A dermoscopic image of a skin lesion.
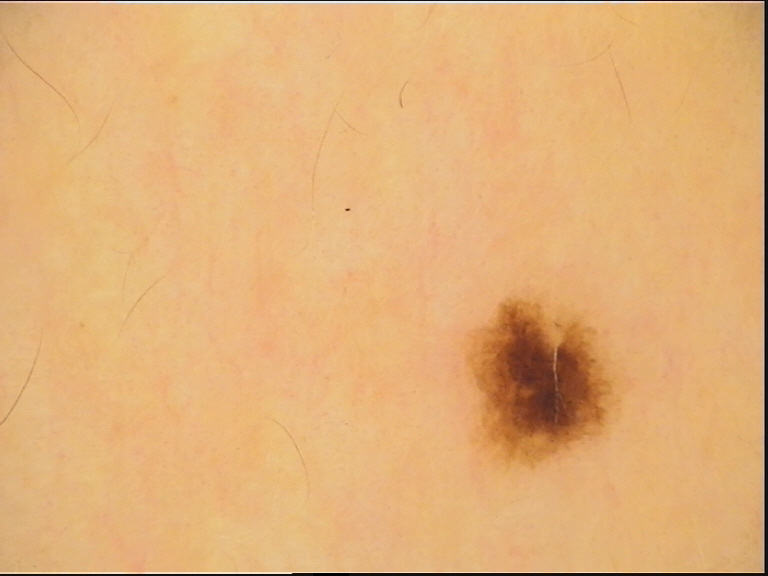class = dysplastic junctional nevus (expert consensus).